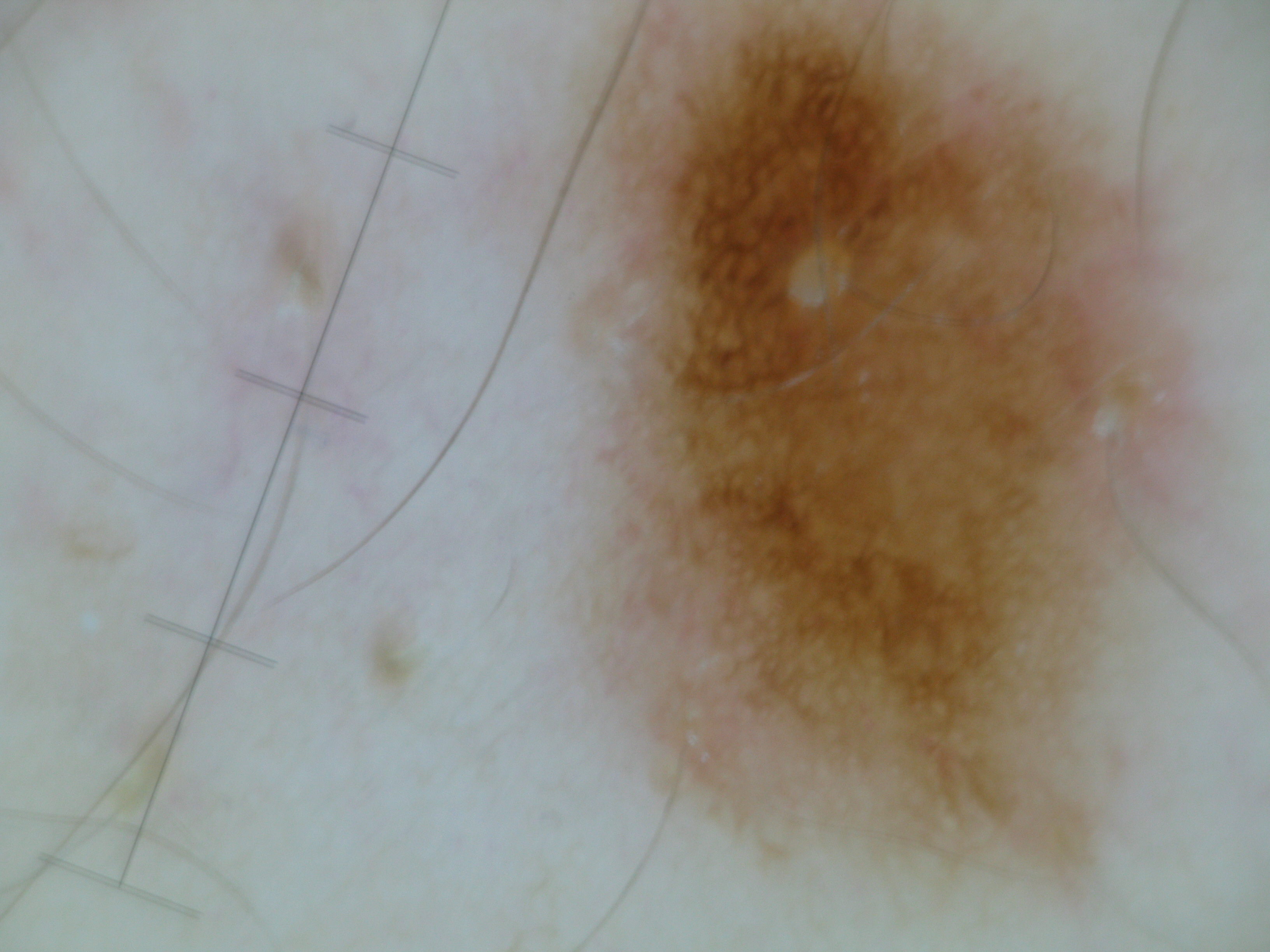Conclusion:
Diagnosed as a dysplastic junctional nevus.